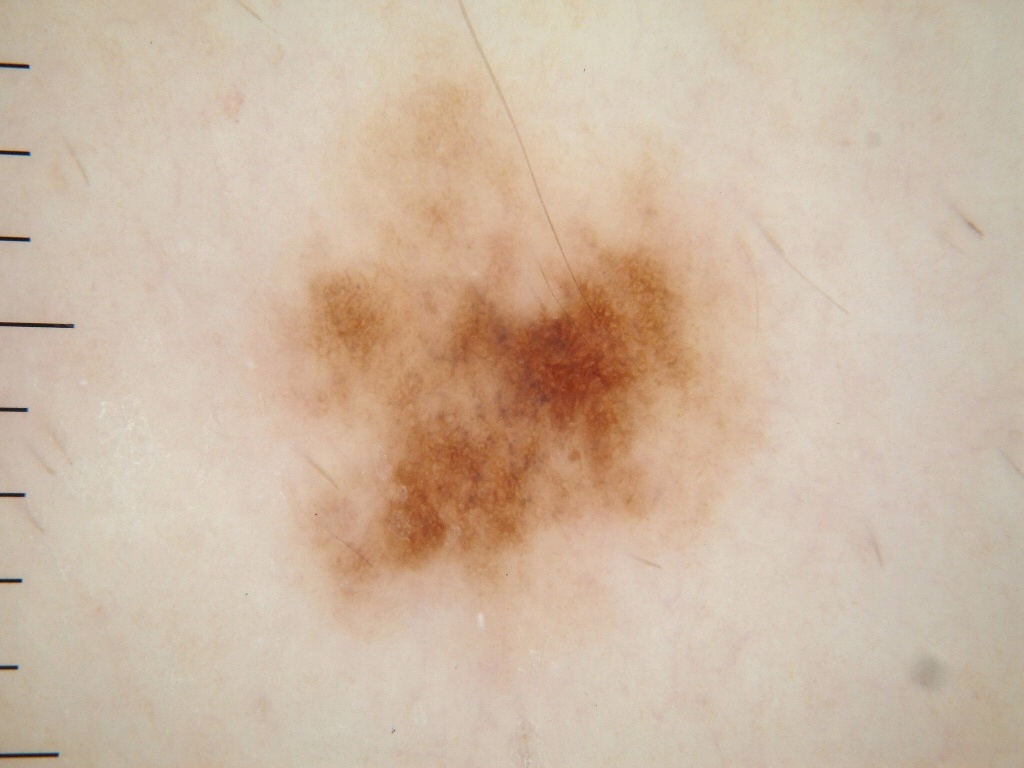<dermoscopy>
  <patient>
    <sex>female</sex>
    <age_approx>30</age_approx>
  </patient>
  <image>
    <modality>dermoscopy</modality>
  </image>
  <dermoscopic_features>
    <present>pigment network</present>
    <absent>streaks, milia-like cysts, globules, negative network</absent>
  </dermoscopic_features>
  <lesion_location>
    <bbox_xyxy>244, 34, 774, 661</bbox_xyxy>
  </lesion_location>
  <diagnosis>
    <name>melanocytic nevus</name>
    <malignancy>benign</malignancy>
    <lineage>melanocytic</lineage>
    <provenance>clinical</provenance>
  </diagnosis>
</dermoscopy>